The photograph was taken at an angle — 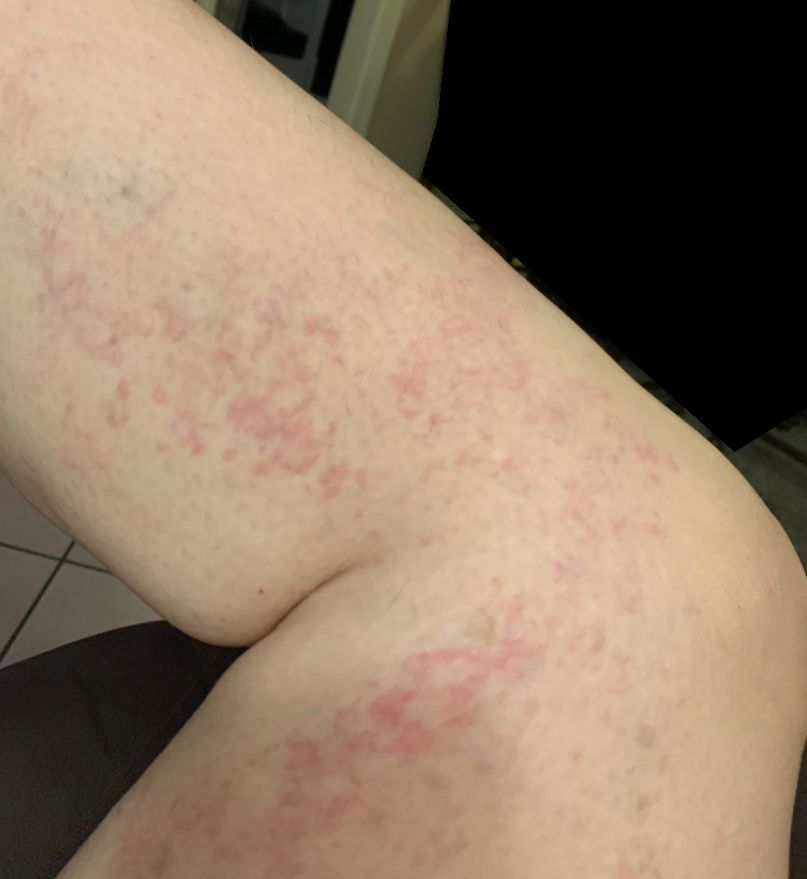Q: What conditions are considered?
A: Urticaria (possible); Allergic Contact Dermatitis (possible)